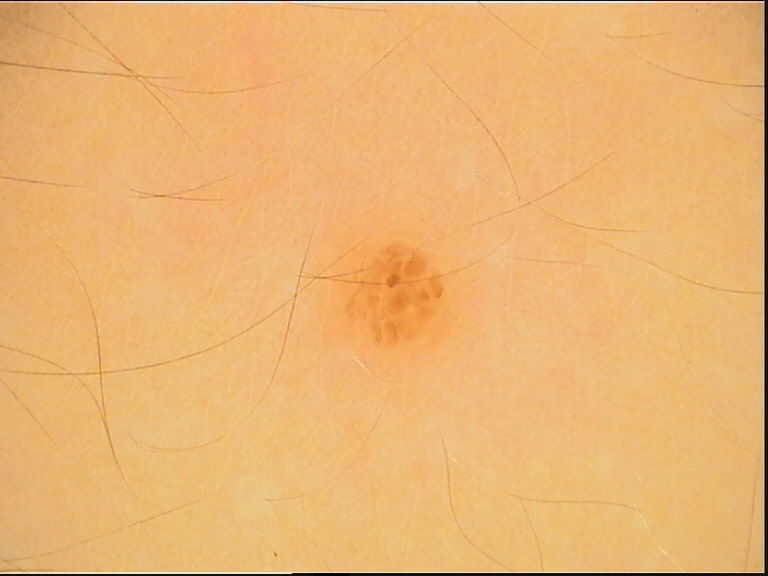image: dermoscopy
lesion_type:
  main_class: banal
  pattern: dermal
diagnosis:
  name: dermal nevus
  code: db
  malignancy: benign
  super_class: melanocytic
  confirmation: expert consensus